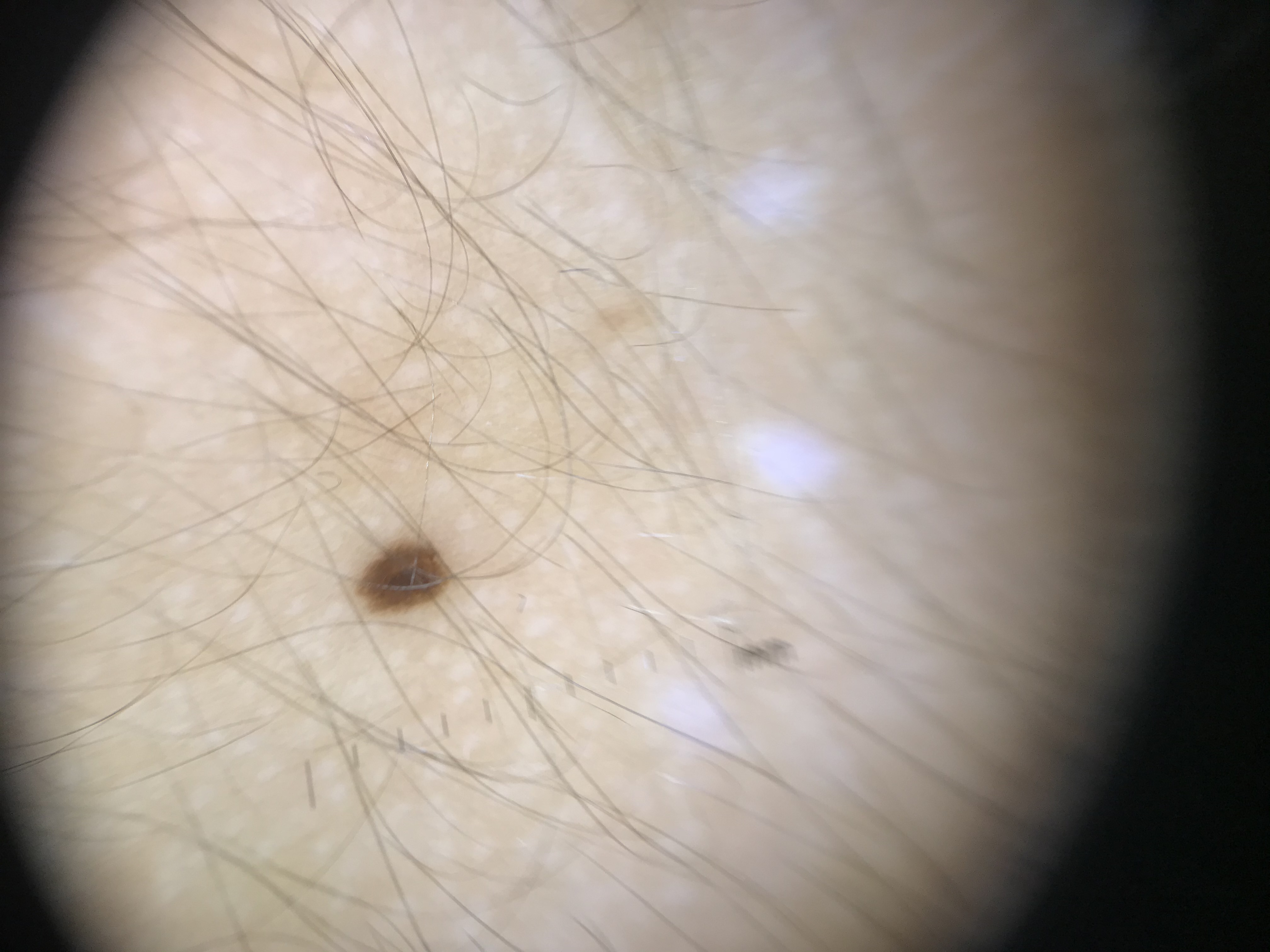imaging — dermoscopy
class — junctional nevus (expert consensus)